Close-up view.
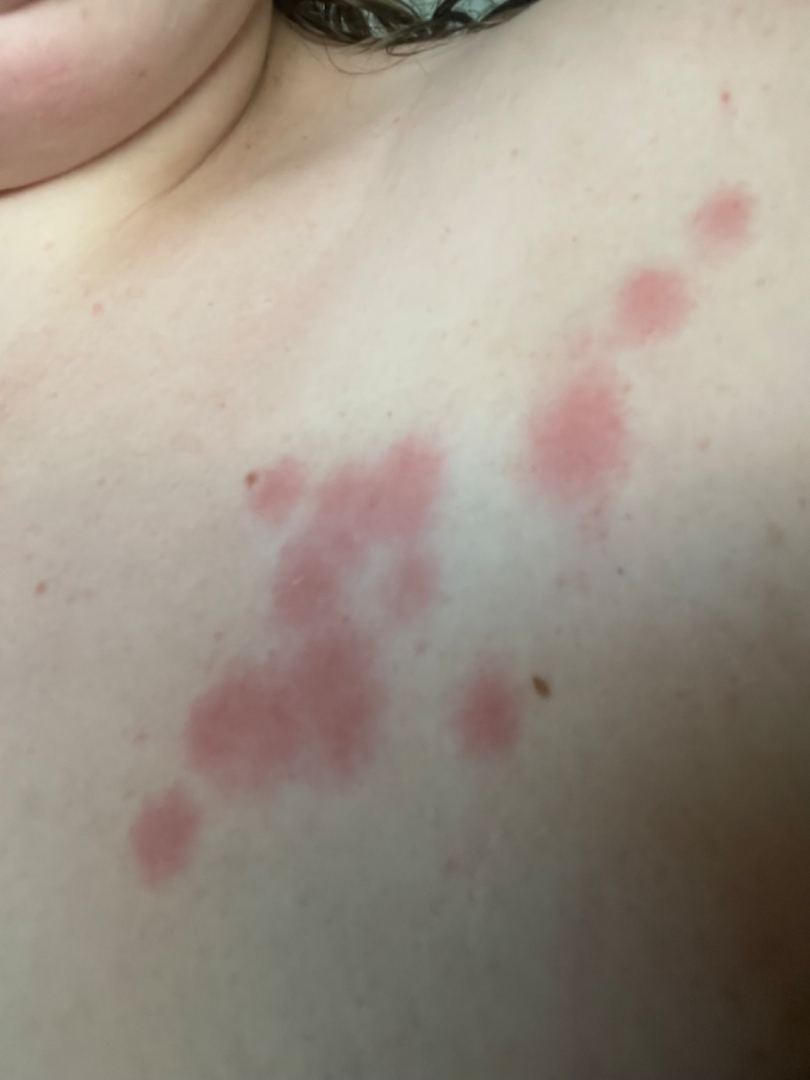Assessment: The reviewing clinician's impression was: the leading consideration is Insect Bite; also on the differential is Urticaria; also raised was Allergic Contact Dermatitis.